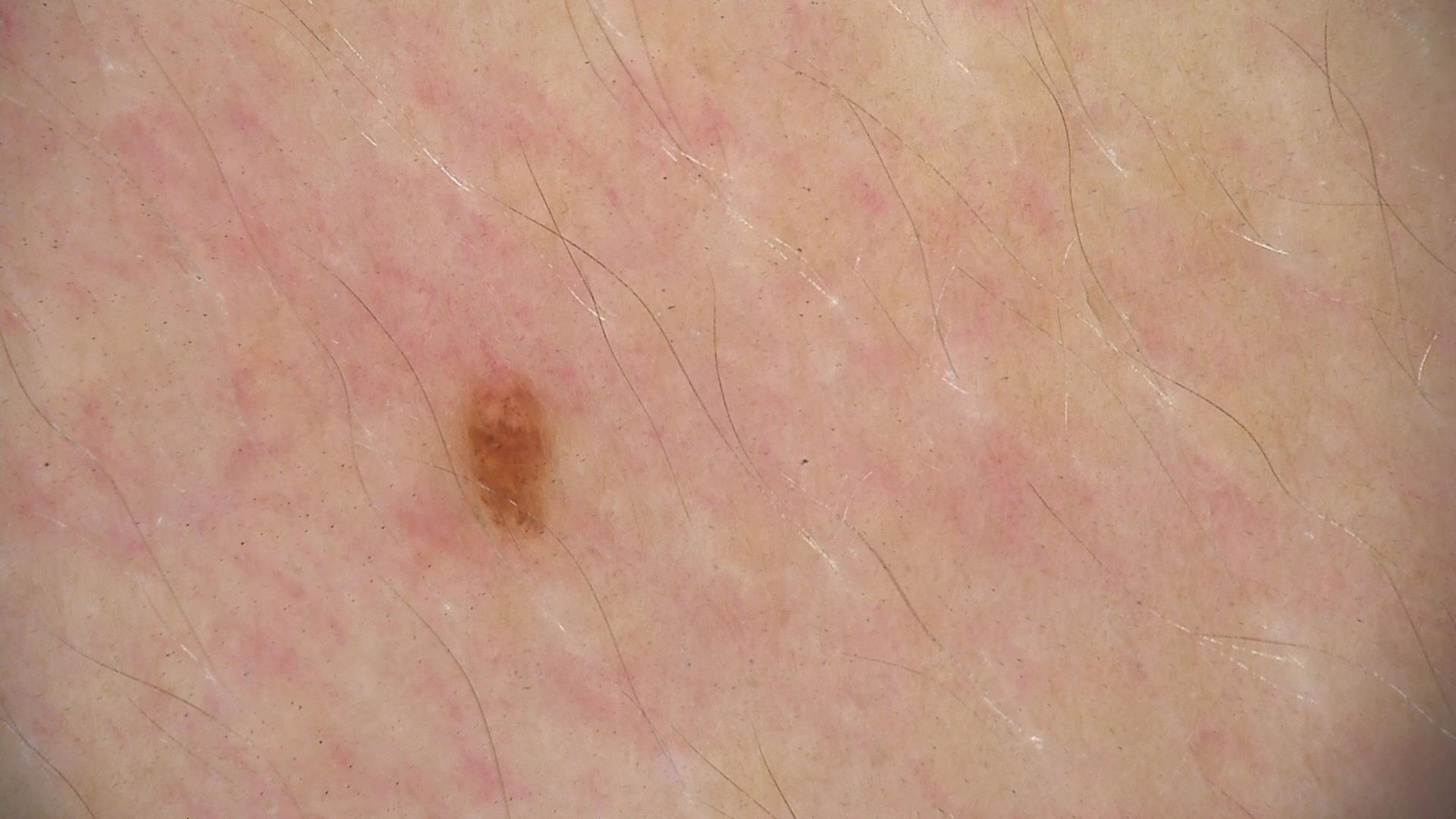A dermoscopic photograph of a skin lesion. The diagnosis was a benign lesion — a dysplastic junctional nevus.